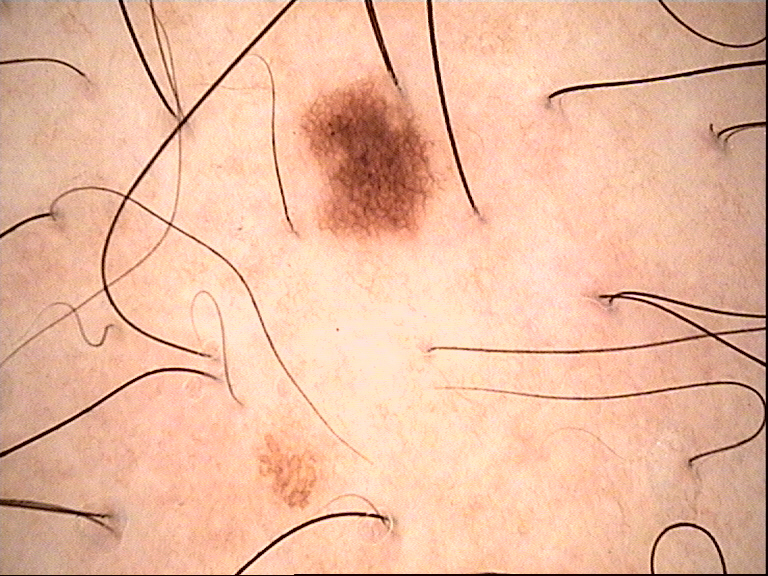A dermoscopic photograph of a skin lesion.
The diagnosis was a banal lesion — a junctional nevus.